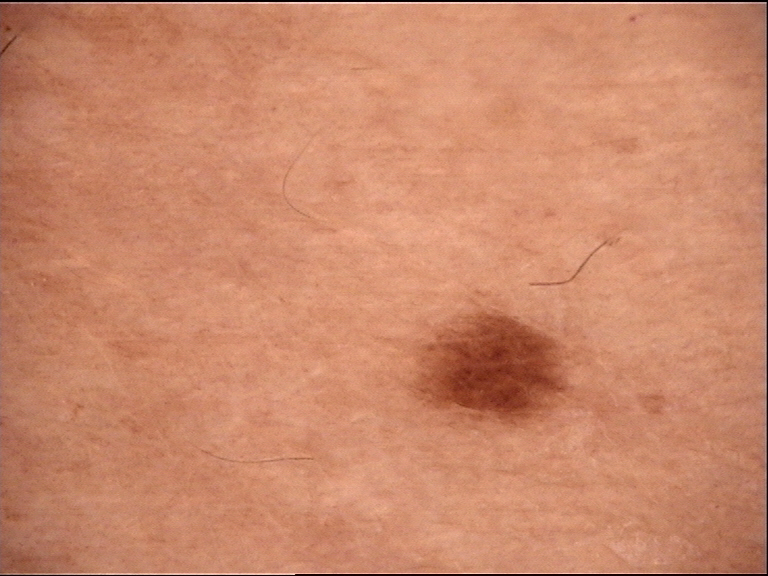A dermoscopic photograph of a skin lesion.
Classified as a dysplastic junctional nevus.